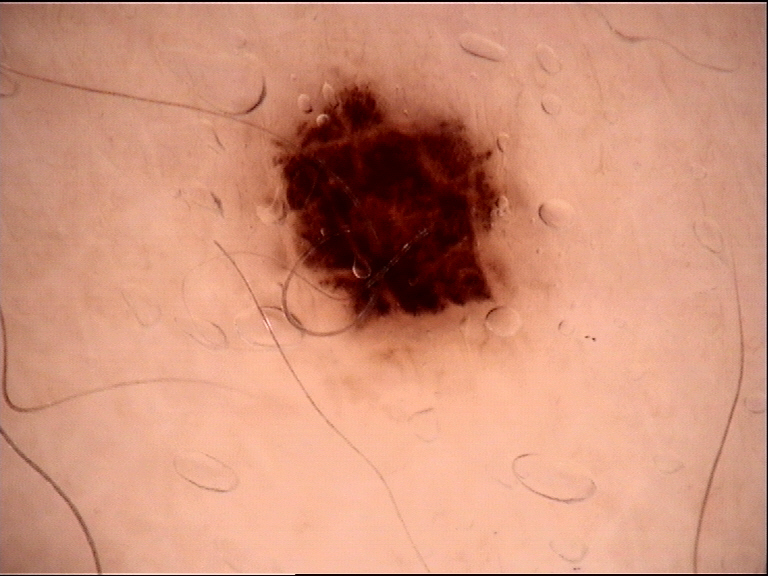Findings: Dermoscopy of a skin lesion. Conclusion: Classified as a dysplastic junctional nevus.